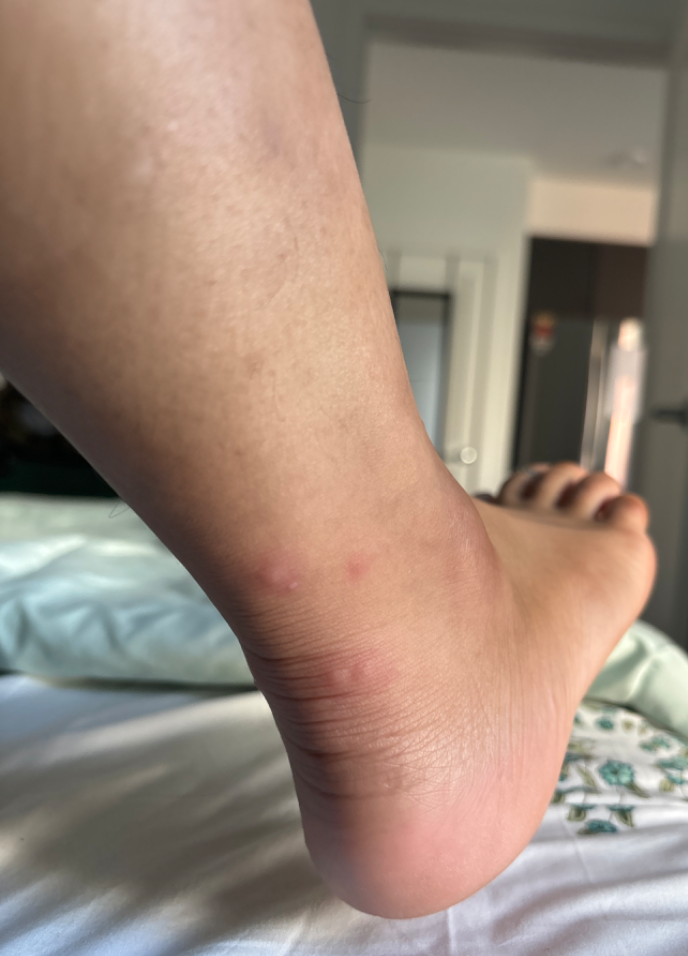Q: Constitutional symptoms?
A: none reported
Q: Anatomic location?
A: top or side of the foot and leg
Q: How does the patient describe it?
A: acne
Q: How long has this been present?
A: about one day
Q: Reported symptoms?
A: itching
Q: Image view?
A: at a distance
Q: How does the lesion feel?
A: raised or bumpy
Q: What conditions are considered?
A: consistent with Insect Bite